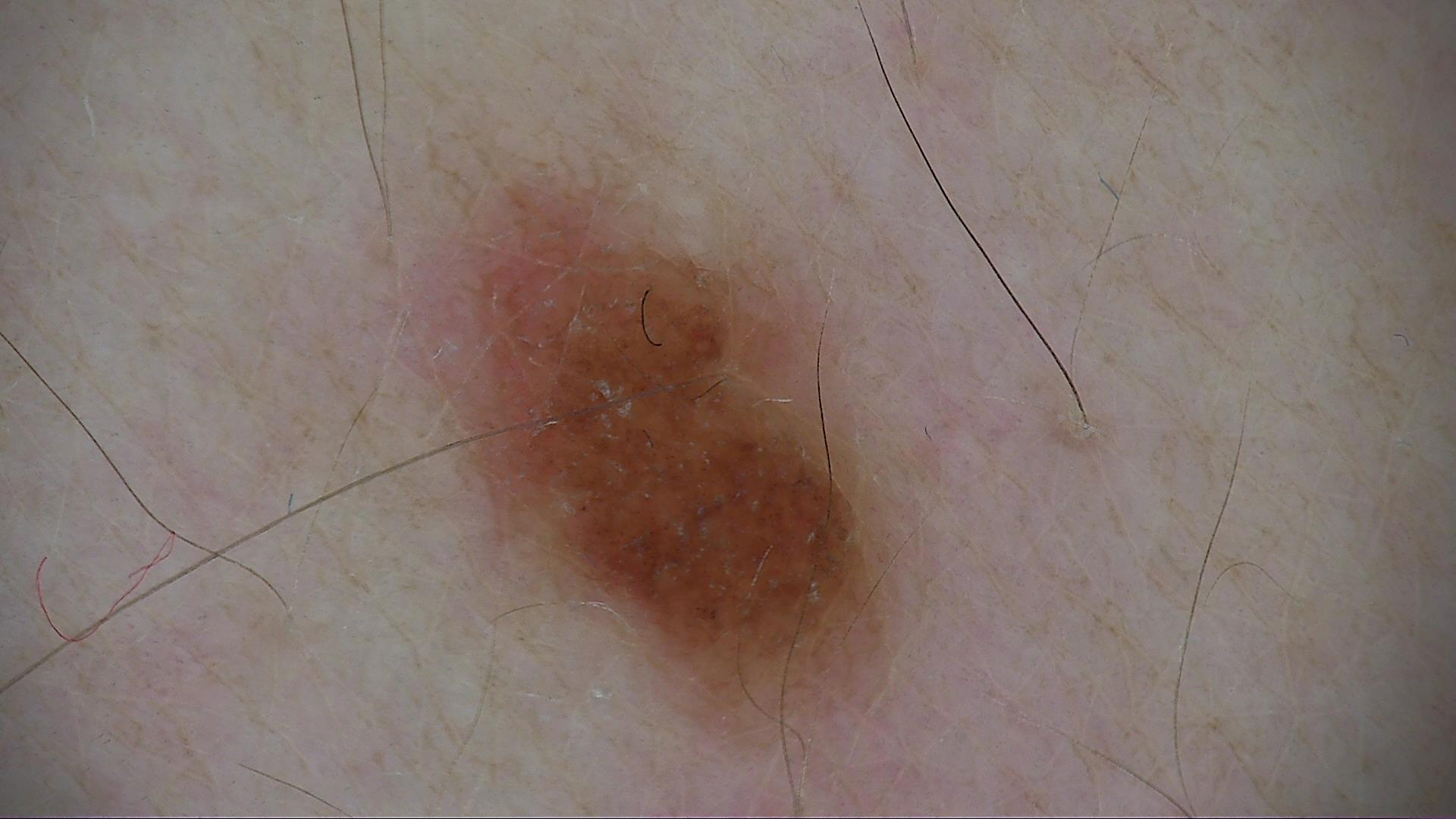Findings:
A dermoscopic image of a skin lesion. The architecture is that of a banal lesion.
Conclusion:
The diagnostic label was a compound nevus.